The head or neck is involved. The condition has been present for about one day. The patient considered this a rash. This image was taken at an angle. Skin tone: Fitzpatrick skin type II. Female patient, age 18–29. Associated systemic symptoms include mouth sores. Symptoms reported: itching and bothersome appearance. The lesion is described as raised or bumpy — 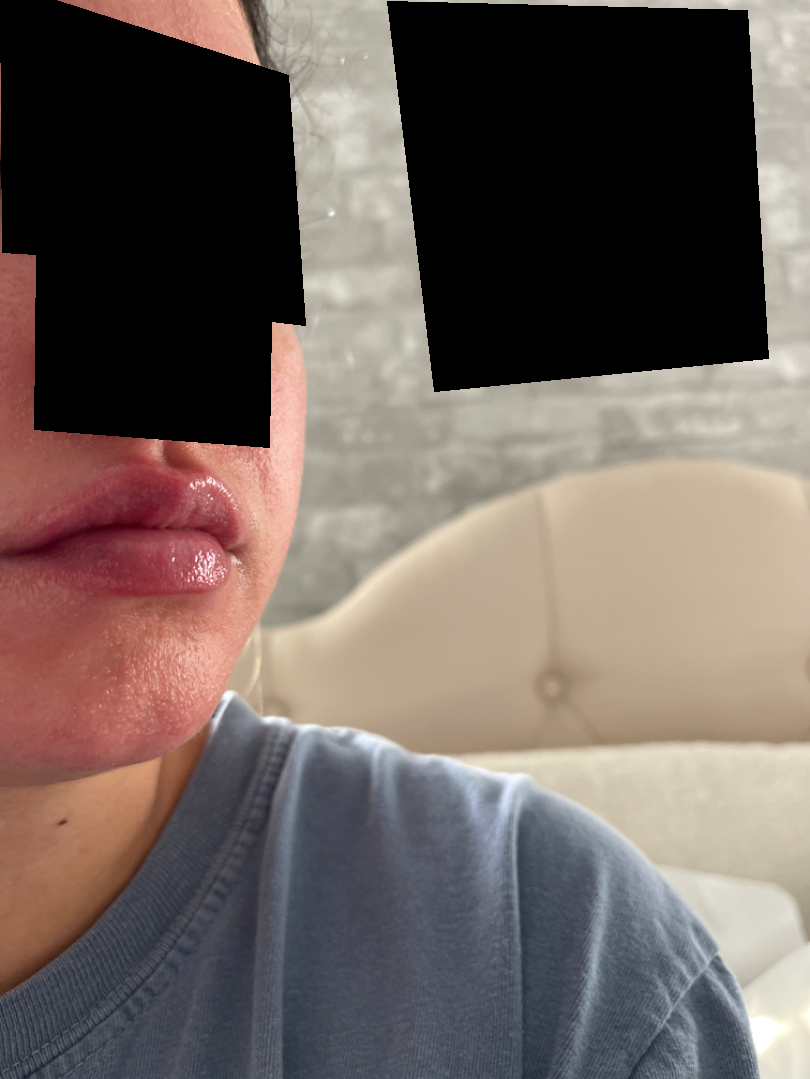Findings:
* assessment: Allergic Contact Dermatitis (weight 0.64); Eczema (weight 0.09); Keratosis pilaris (weight 0.09); Acne (weight 0.09); Rosacea (weight 0.09)